A dermoscopic close-up of a skin lesion; the subject is a male aged 58-62 — 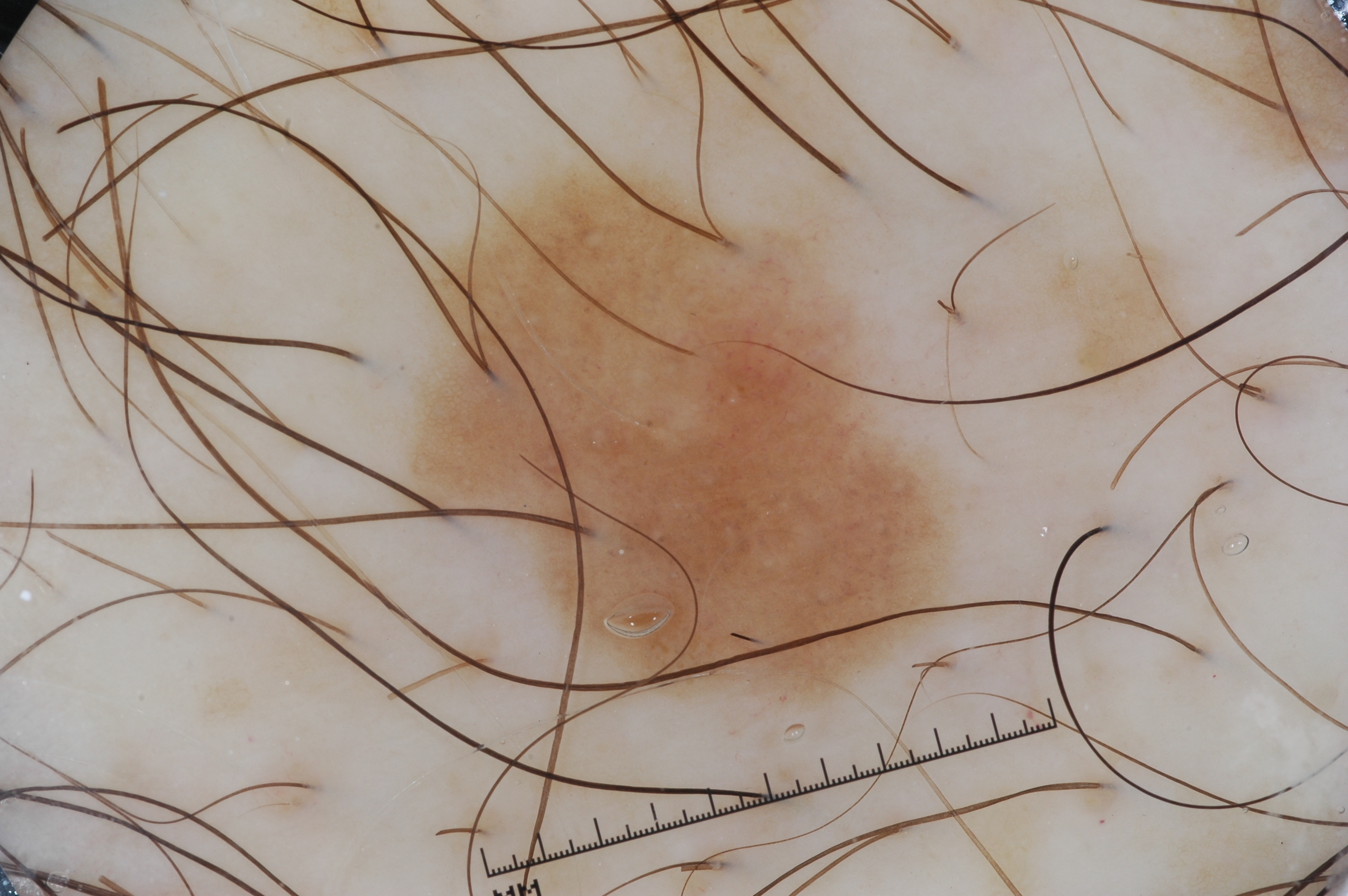Dermoscopically, the lesion shows pigment network and milia-like cysts.
With coordinates (x1, y1, x2, y2), the lesion is bounded by 387, 134, 977, 739.
The diagnostic assessment was a melanocytic nevus.